Reported lesion symptoms include bothersome appearance and itching. The patient considered this a rash. The lesion involves the arm. An image taken at a distance. The lesion is described as raised or bumpy. The patient reports the condition has been present for less than one week.
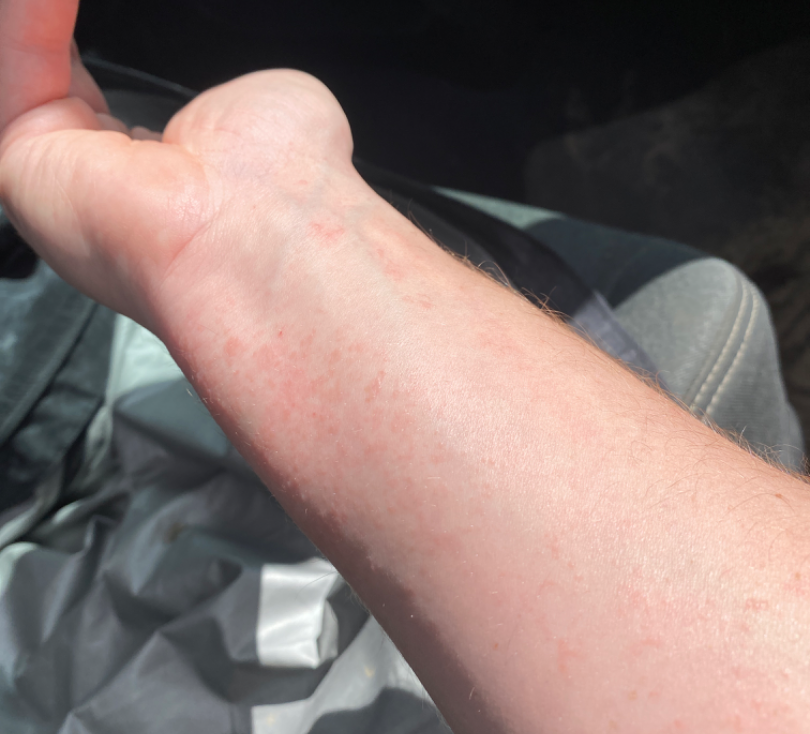Consistent with Acute dermatitis, NOS.